This image was taken at a distance · the top or side of the foot and leg are involved · reported duration is more than one year · the patient reports darkening, bothersome appearance, burning and itching · the patient reports the lesion is raised or bumpy and rough or flaky · the patient described the issue as a rash — 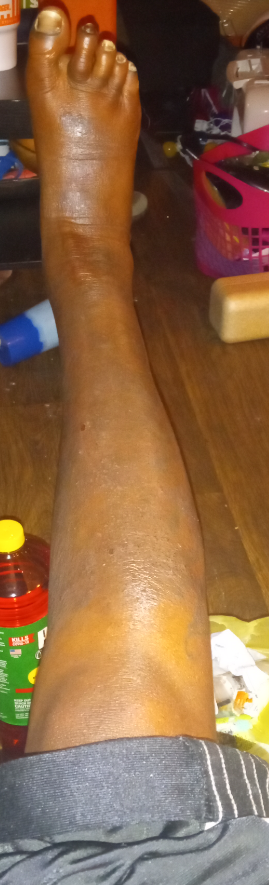Findings:
– assessment — the differential includes Stasis Dermatitis; Eczema; and Contact dermatitis, NOS, with no clear leading consideration